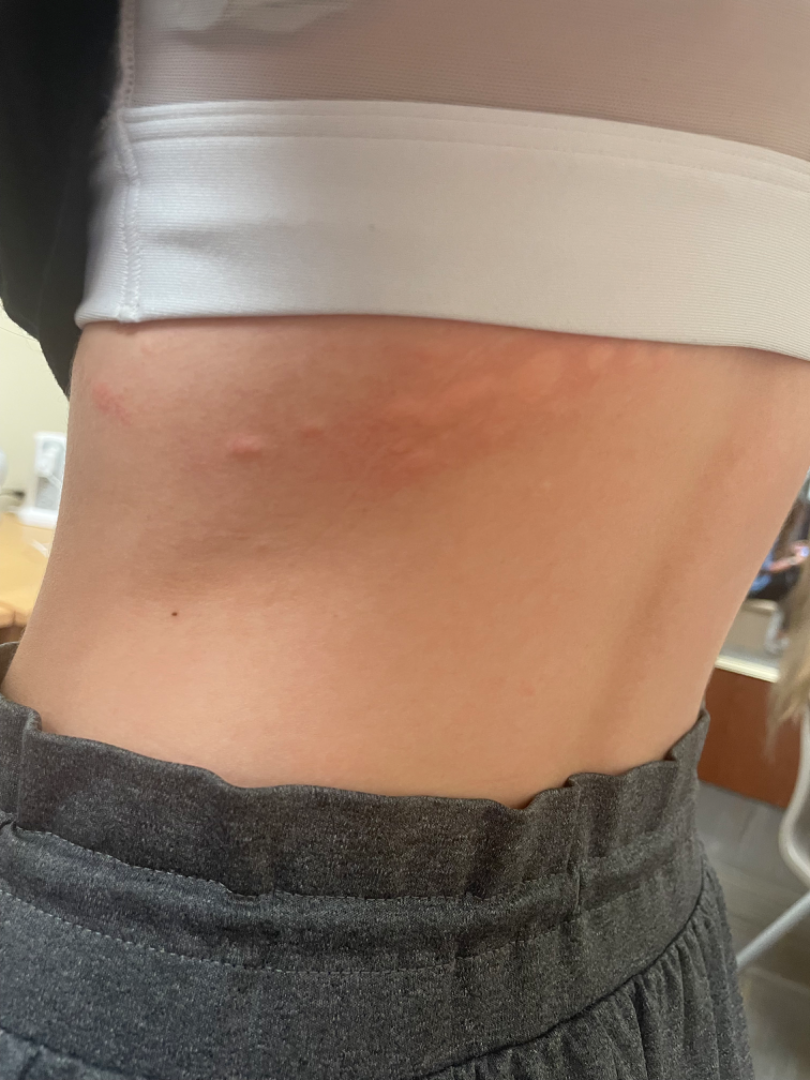Q: What is the differential diagnosis?
A: in keeping with Urticaria